Dermoscopy of a skin lesion: 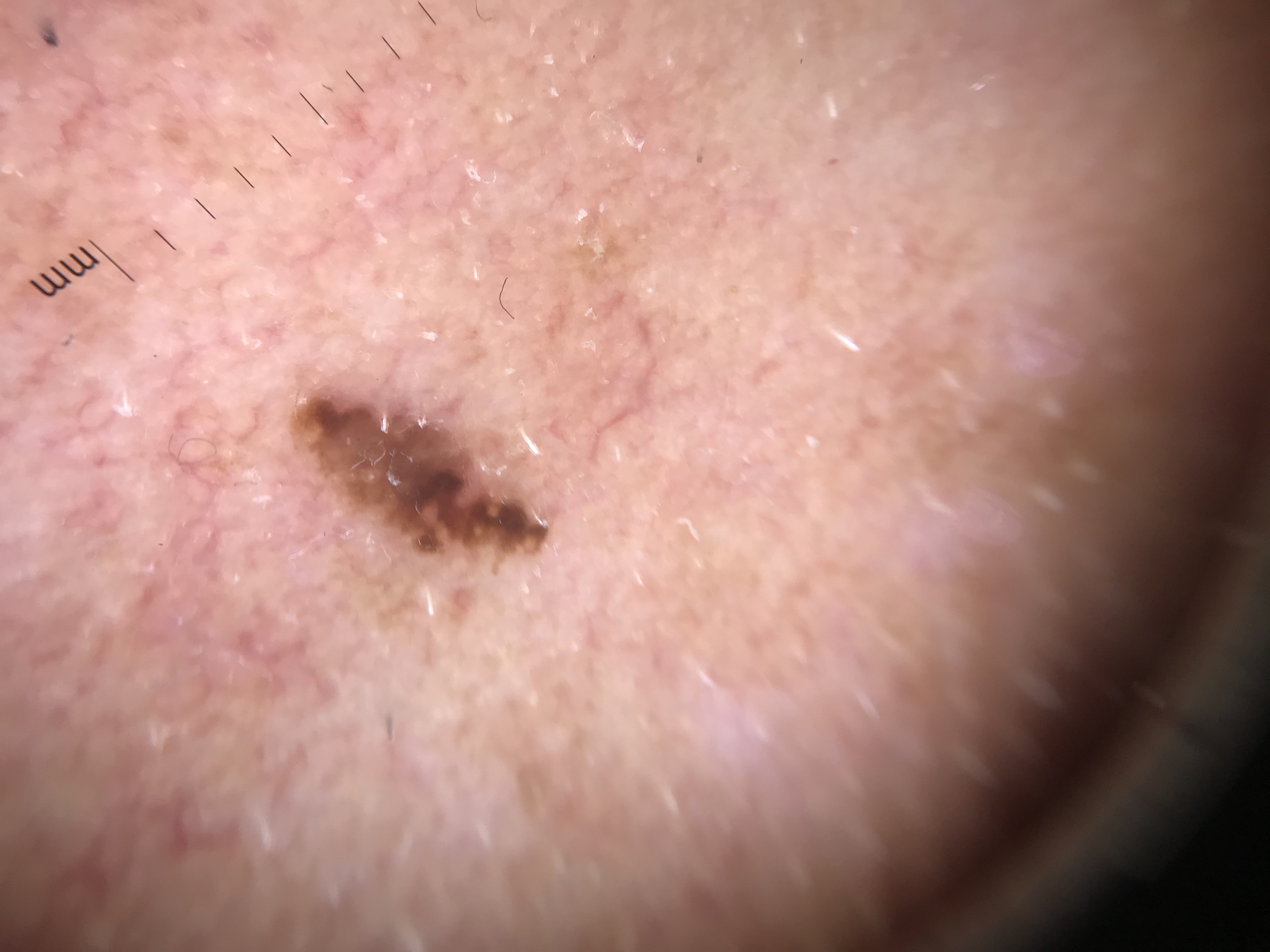assessment: seborrheic keratosis (expert consensus).